Female patient, age 18–29. A close-up photograph. Located on the arm:
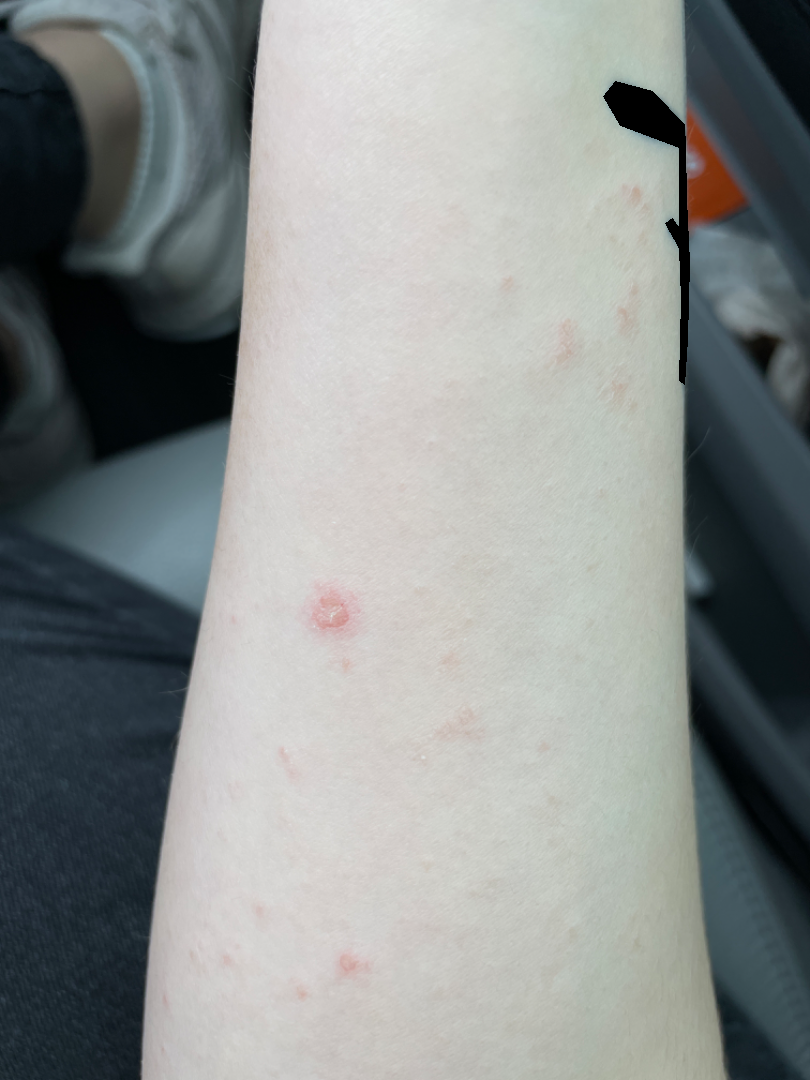Case summary:
– assessment · unable to determine